Reported duration is one to four weeks, the patient notes itching, an image taken at an angle, the patient considered this a rash, the lesion involves the arm, texture is reported as raised or bumpy:
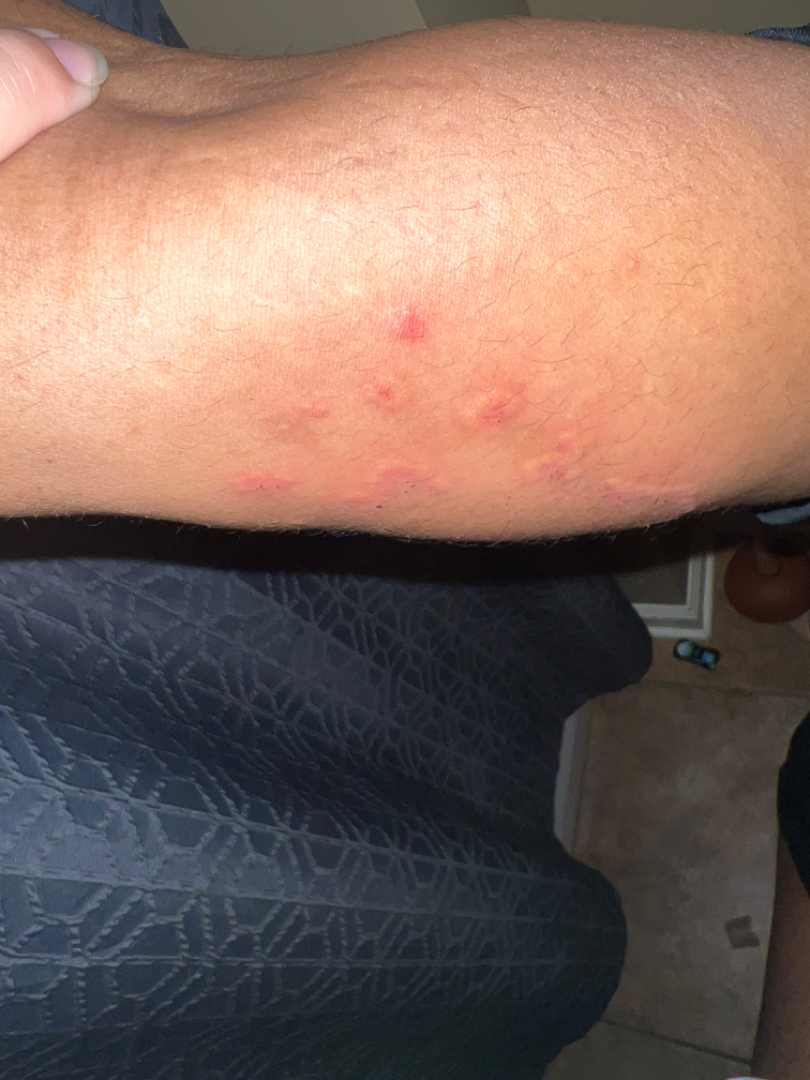On remote review of the image, the primary impression is Leukocytoclastic Vasculitis.